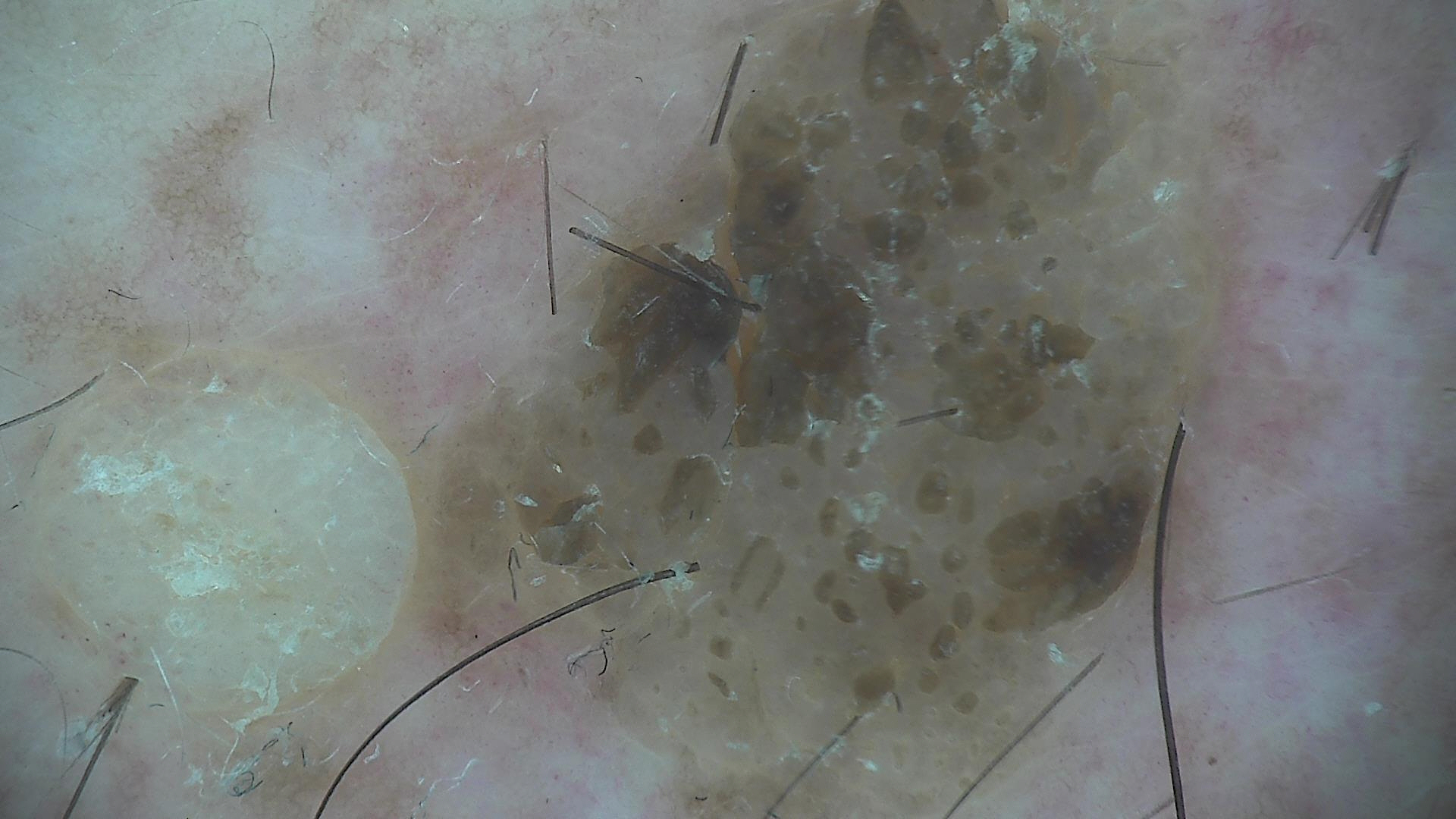image: dermoscopy; diagnosis: seborrheic keratosis (expert consensus).